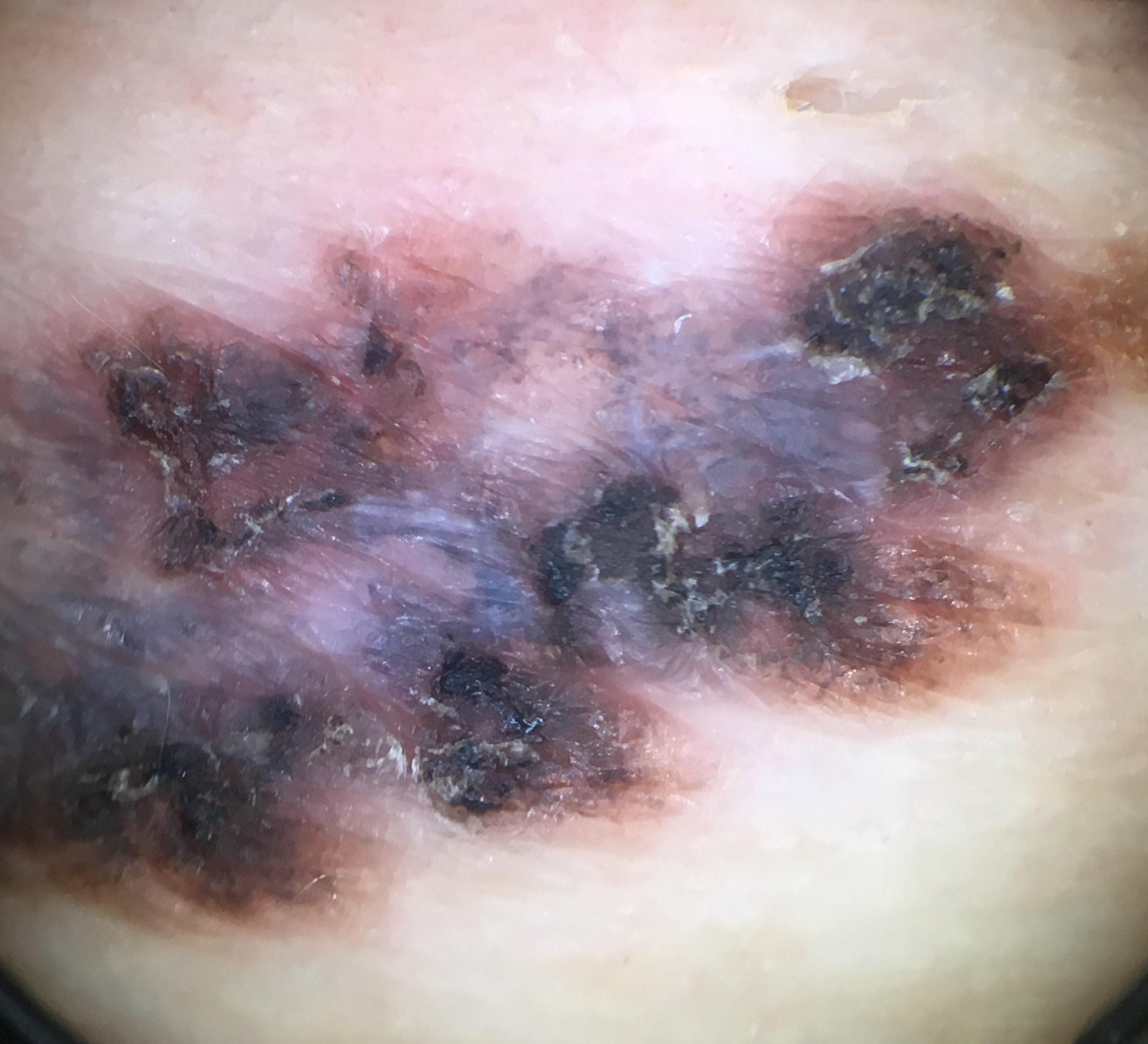FST — II; patient — female, aged 73 to 77; relevant background — a previous melanoma; location — the trunk; diagnostic label — Melanoma (biopsy-proven).